The photo was captured at an angle: 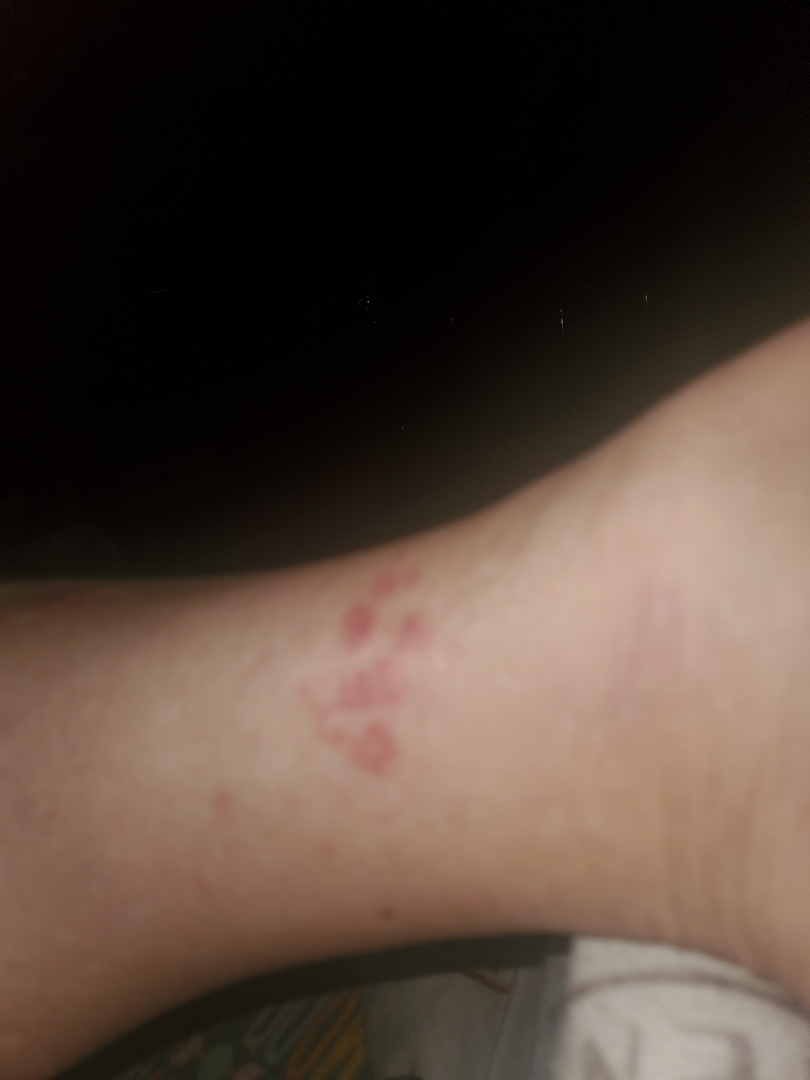Q: Any systemic symptoms?
A: none reported
Q: What is the dermatologist's impression?
A: reviewed remotely by one dermatologist: most likely Insect Bite; also consider Allergic Contact Dermatitis; less likely is Urticaria